The photograph was taken at a distance: 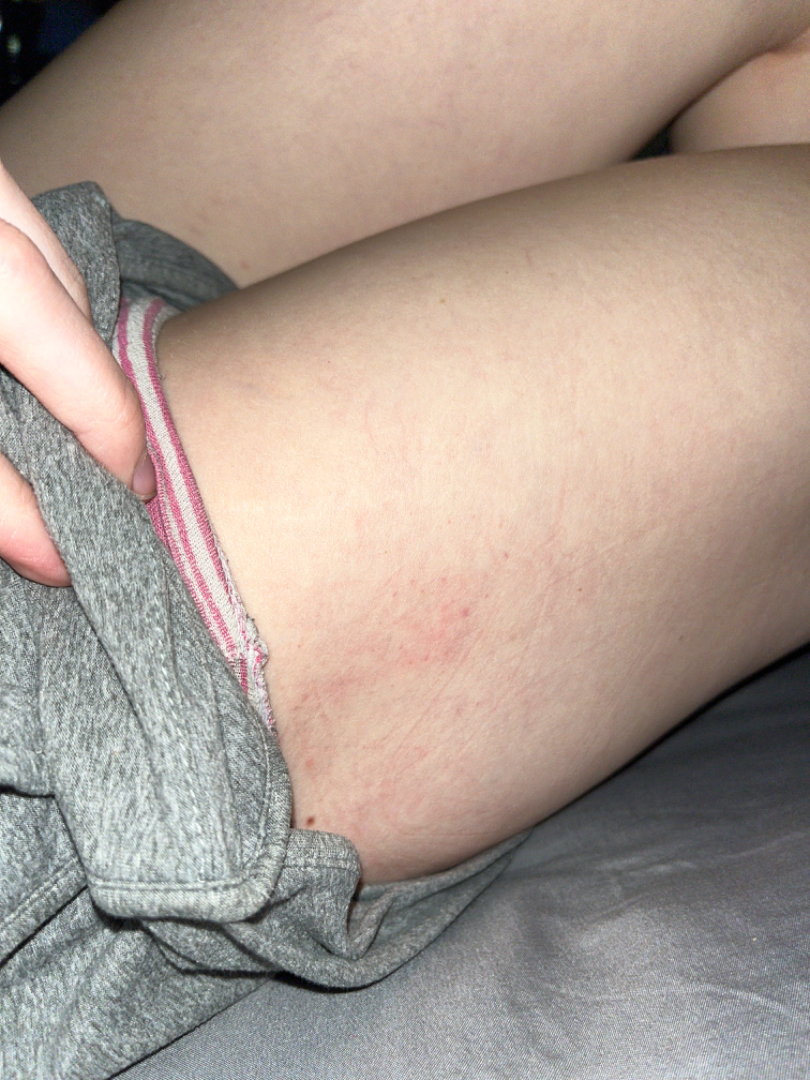patient describes the issue as: a rash
history: about one day
symptoms: itching
skin tone: Fitzpatrick skin type II; lay reviewers estimated MST 2 or 3
surface texture: raised or bumpy
diagnostic considerations: the leading impression is petechiae; also consider ecchymoses